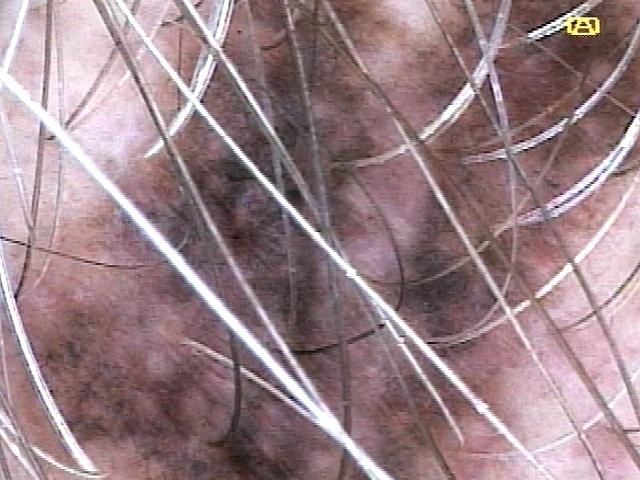Findings:
– subject · male, in their mid-70s
– Fitzpatrick · II
– imaging · dermatoscopic image
– body site · the head or neck
– diagnosis · Melanoma (biopsy-proven)